The photograph was taken at an angle.
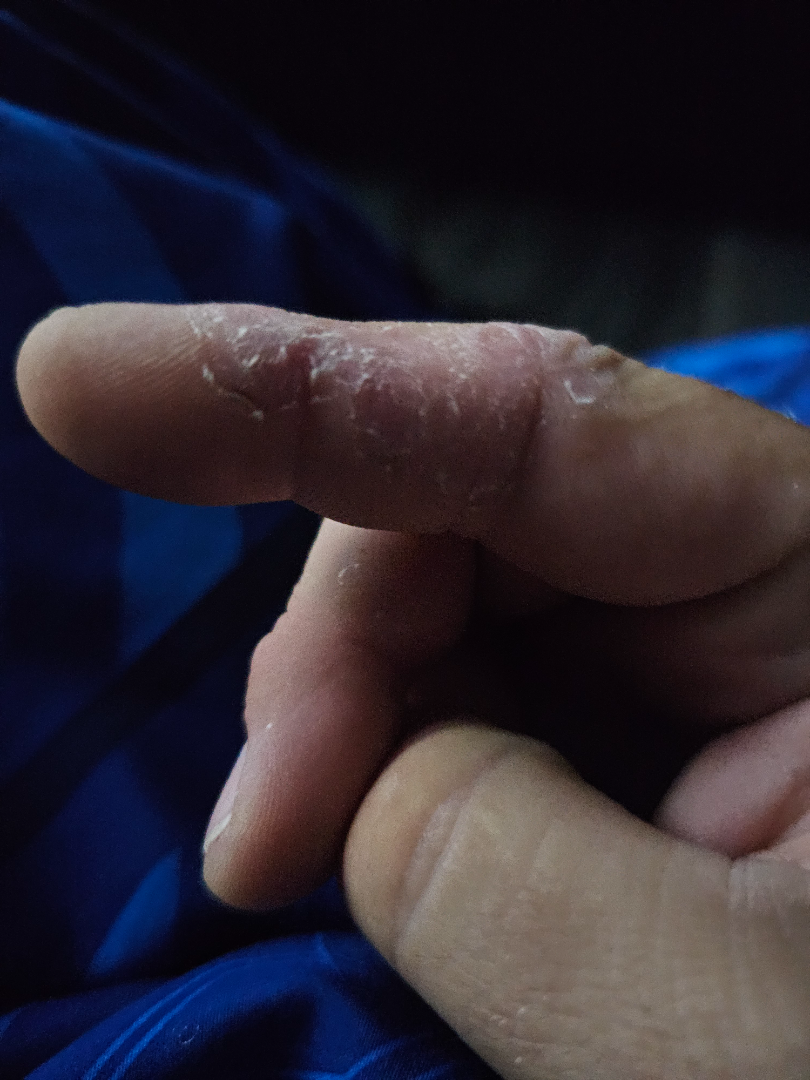differential:
  Eczema: 1.0